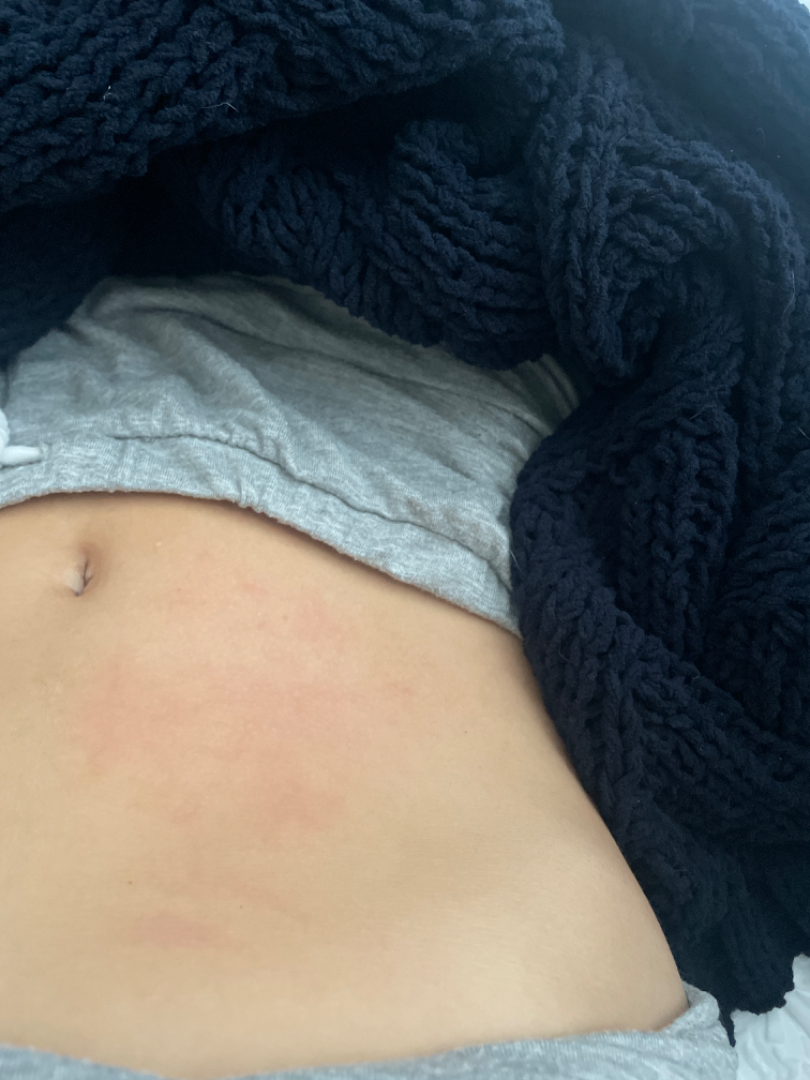Assessment: No differential diagnosis could be assigned on photographic review. Clinical context: Self-categorized by the patient as a rash. The condition has been present for one to four weeks. The patient is female. The affected area is the front of the torso. The contributor notes burning and itching. This image was taken at a distance. Fitzpatrick phototype IV. Texture is reported as raised or bumpy.